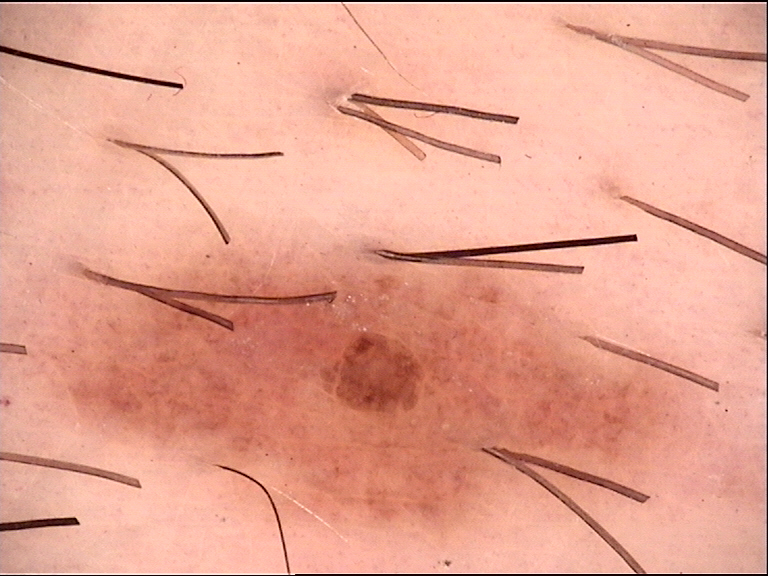  image: dermoscopy
  diagnosis:
    name: dysplastic junctional nevus
    code: jd
    malignancy: benign
    super_class: melanocytic
    confirmation: expert consensus